The lesion involves the arm and leg, this is a close-up image — 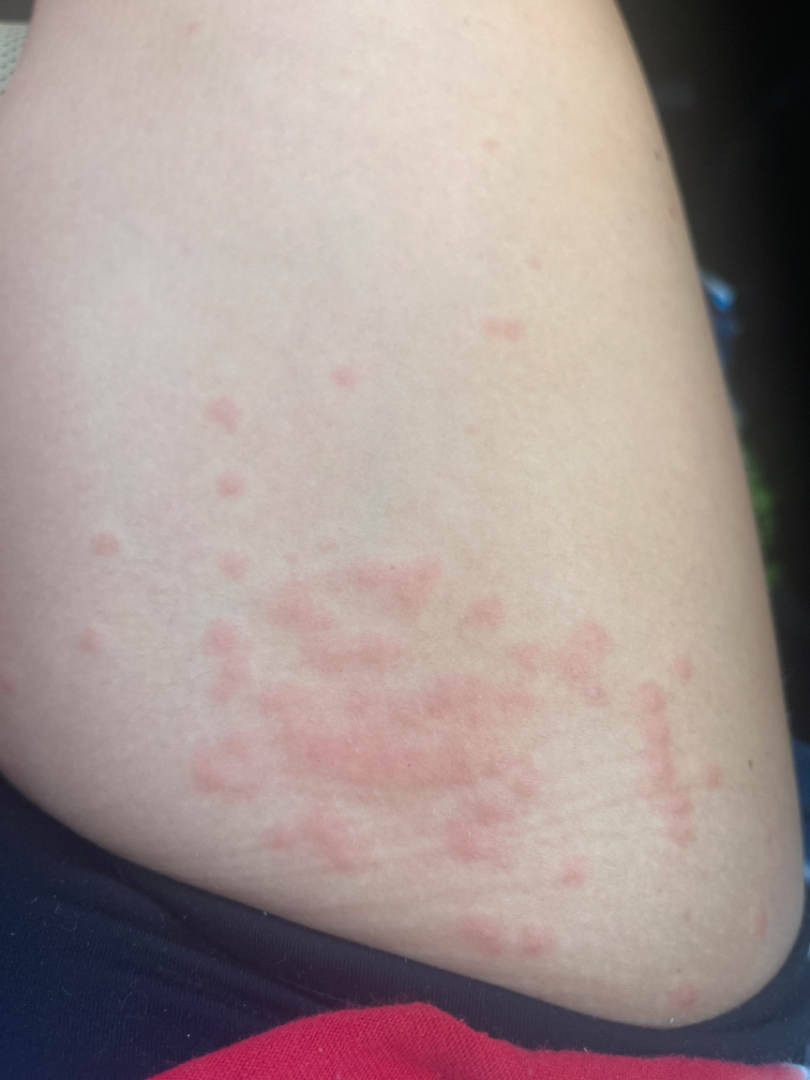assessment = could not be assessed.